A female subject aged approximately 80. A skin lesion imaged with a dermatoscope.
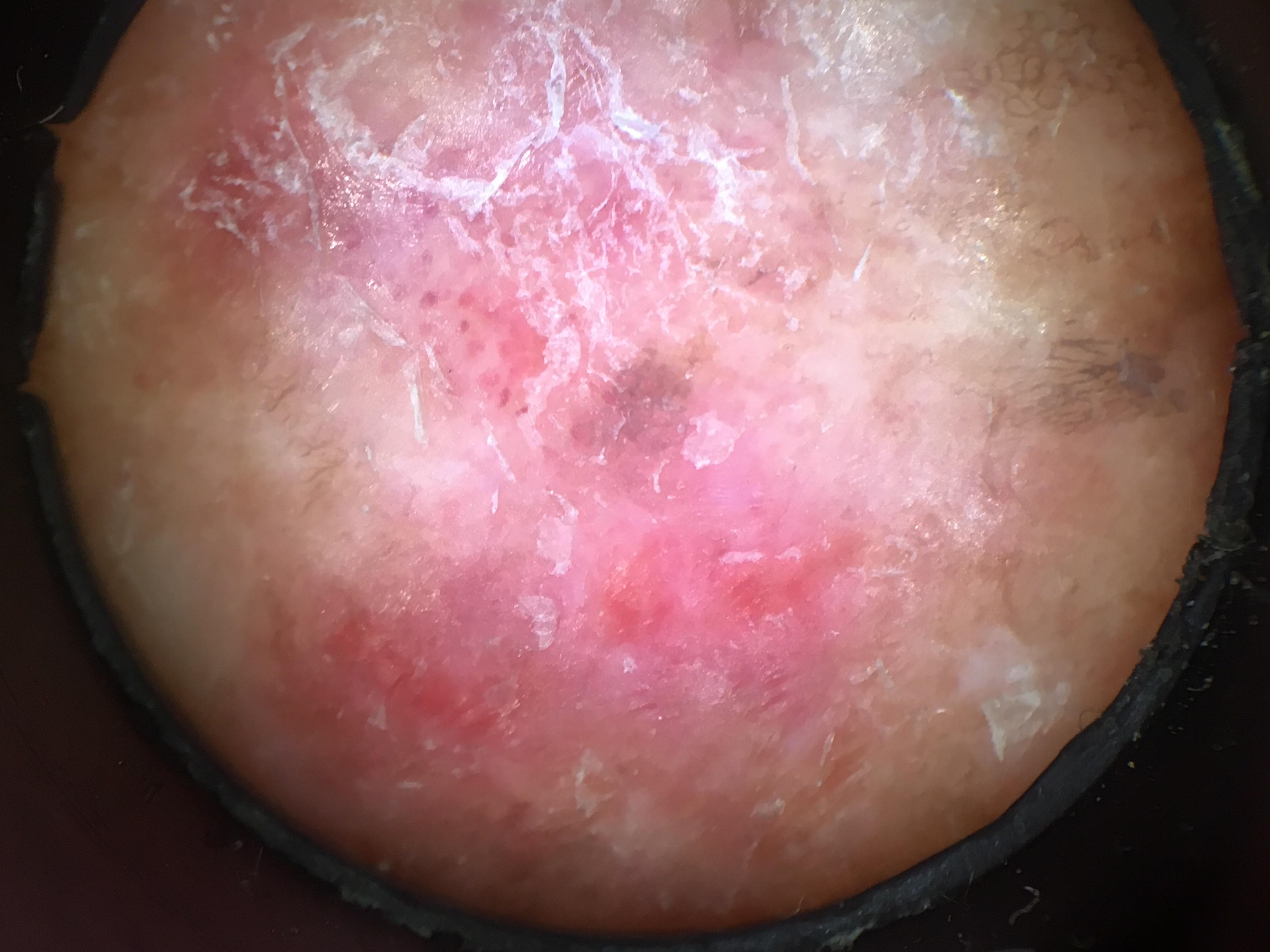anatomic site = a lower extremity; diagnosis = Basal cell carcinoma (biopsy-proven).